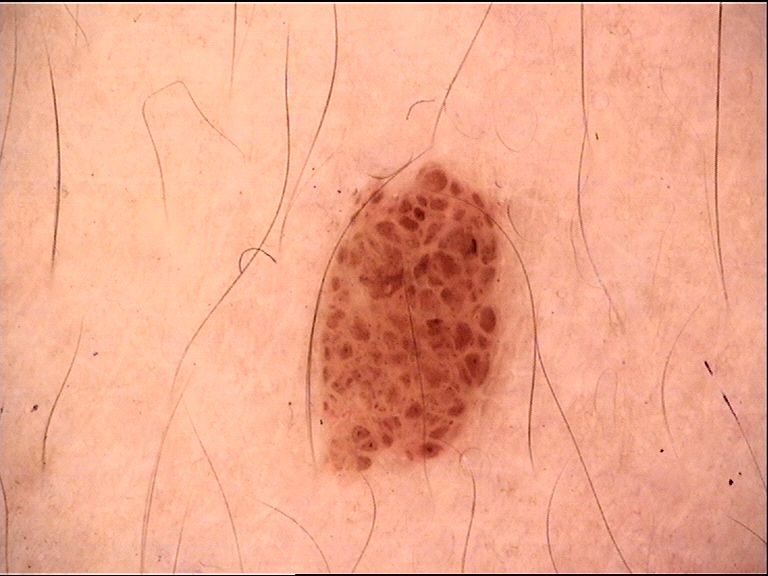diagnosis — compound nevus (expert consensus).